An image taken at a distance. The lesion involves the leg. The subject is 18–29, female:
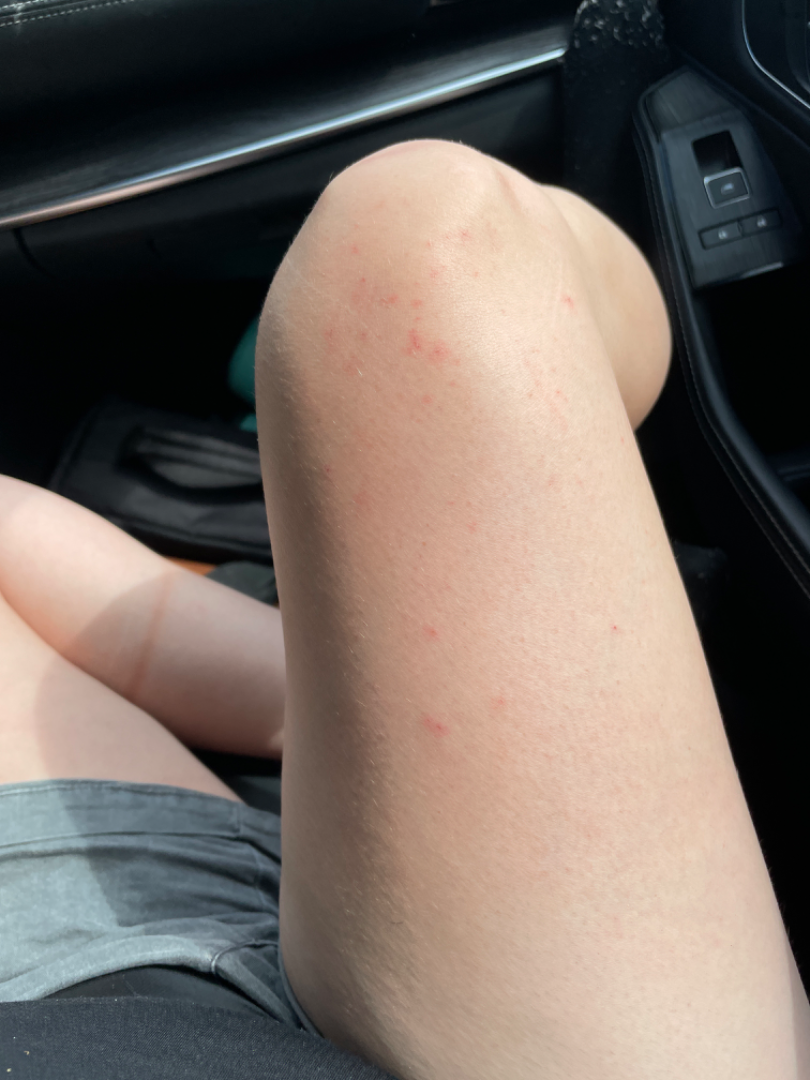differential:
  leading:
    - Folliculitis
  considered:
    - Eczema